Dermoscopy of a skin lesion: 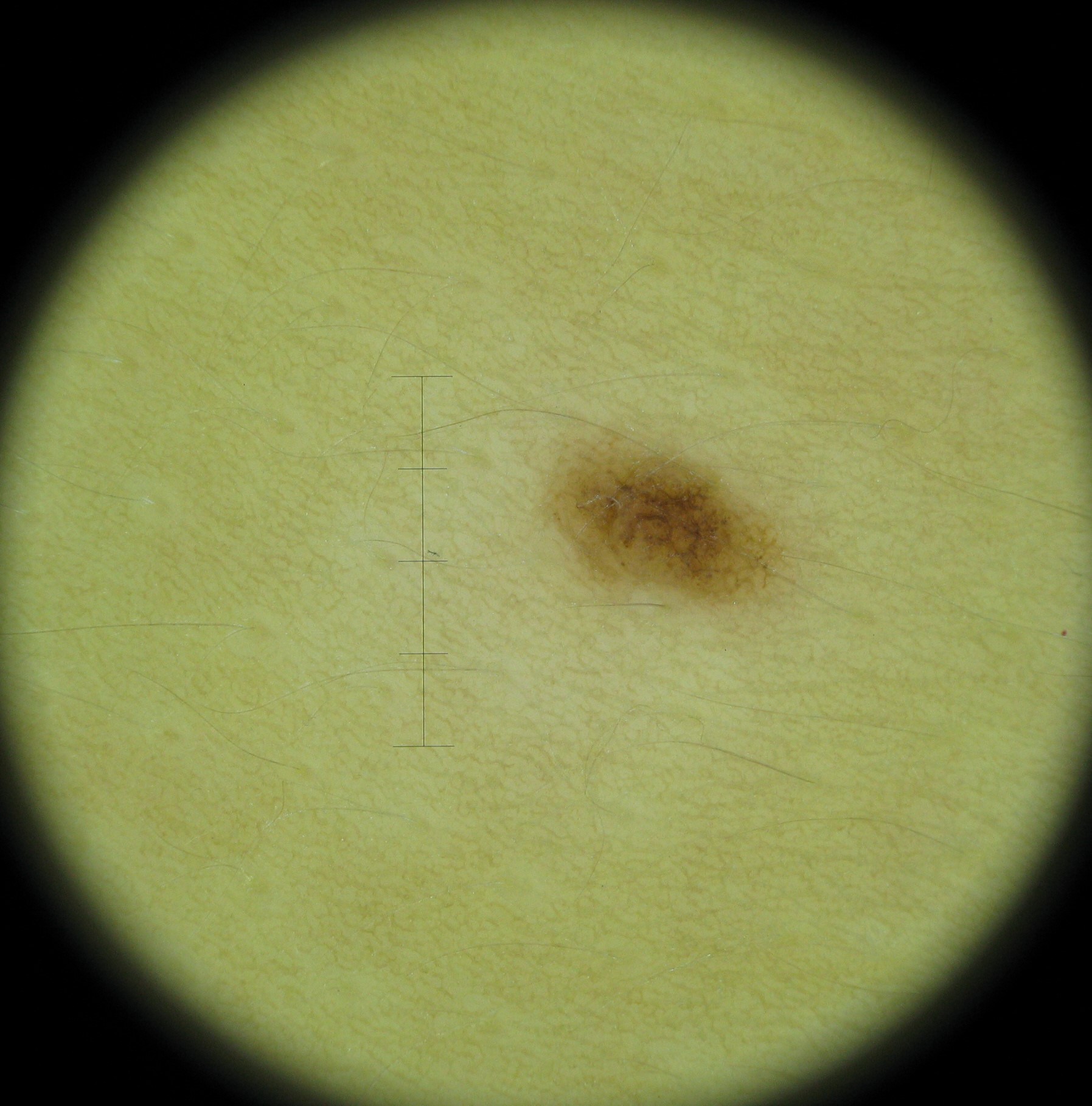Classified as a dysplastic junctional nevus.